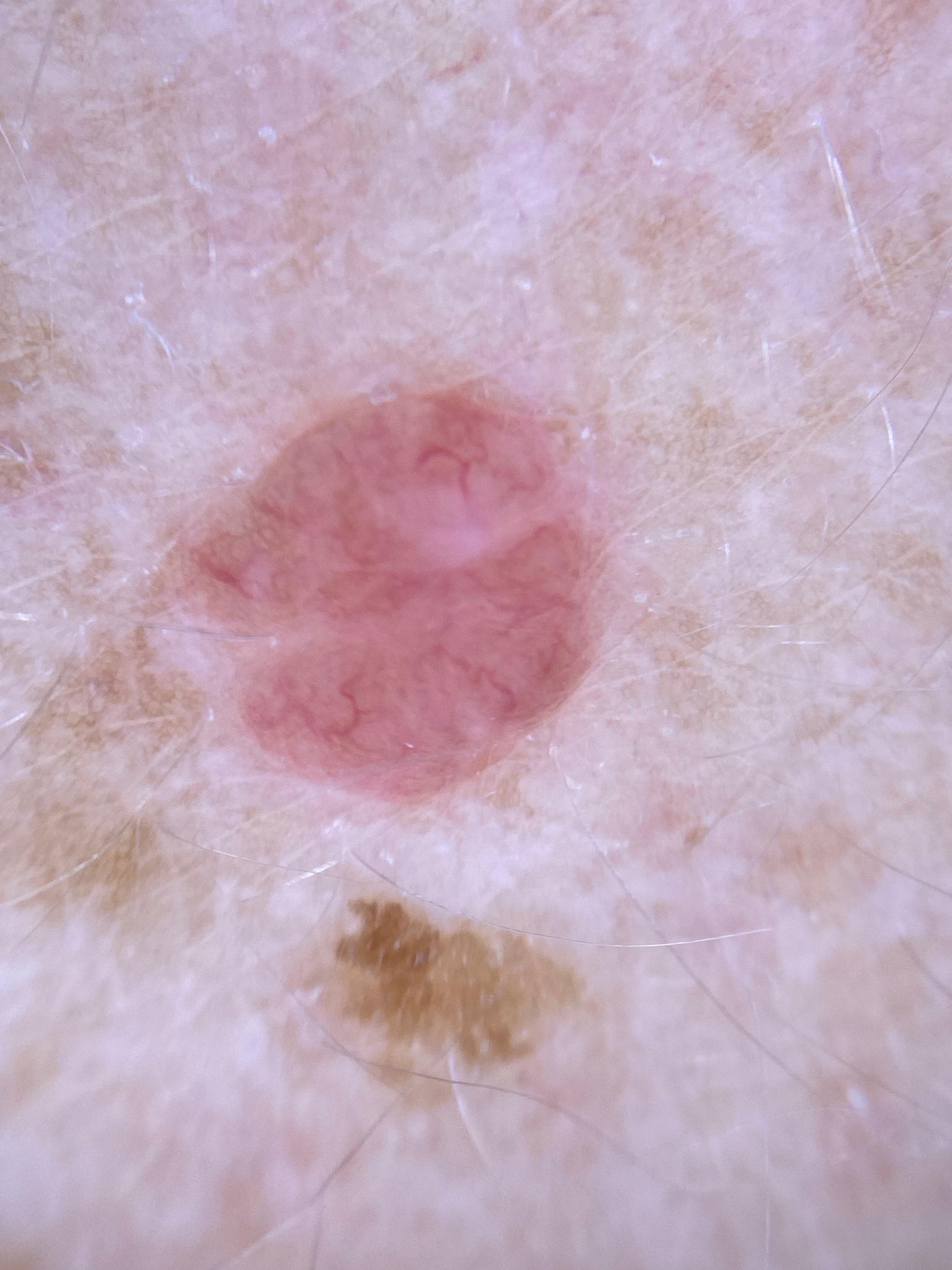relevant background — no prior melanoma and no first-degree relative with melanoma
subject — female, aged around 60
diagnosis — Nevus (biopsy-proven)